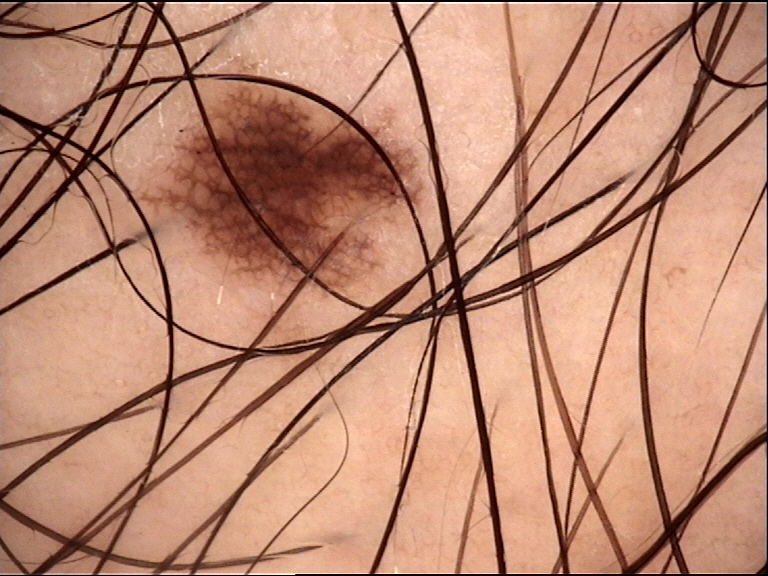A dermoscopy image of a single skin lesion.
Diagnosed as a banal lesion — a junctional nevus.